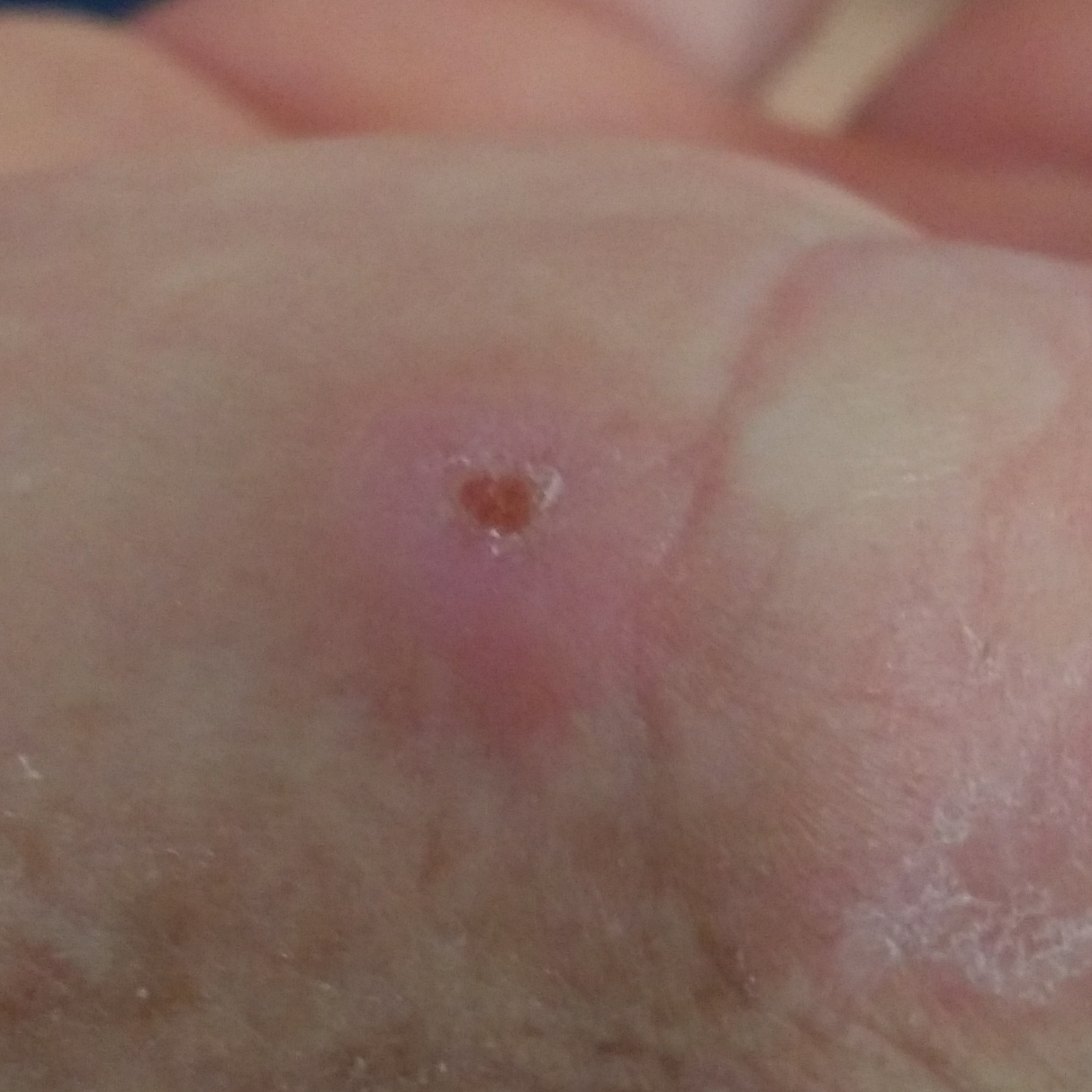Case:
- image type · clinical photo
- subject · female, 57 years old
- region · a hand
- lesion diameter · 14x13 mm
- patient-reported symptoms · change in appearance, growth, elevation, pain / no bleeding
- pathology · squamous cell carcinoma (biopsy-proven)